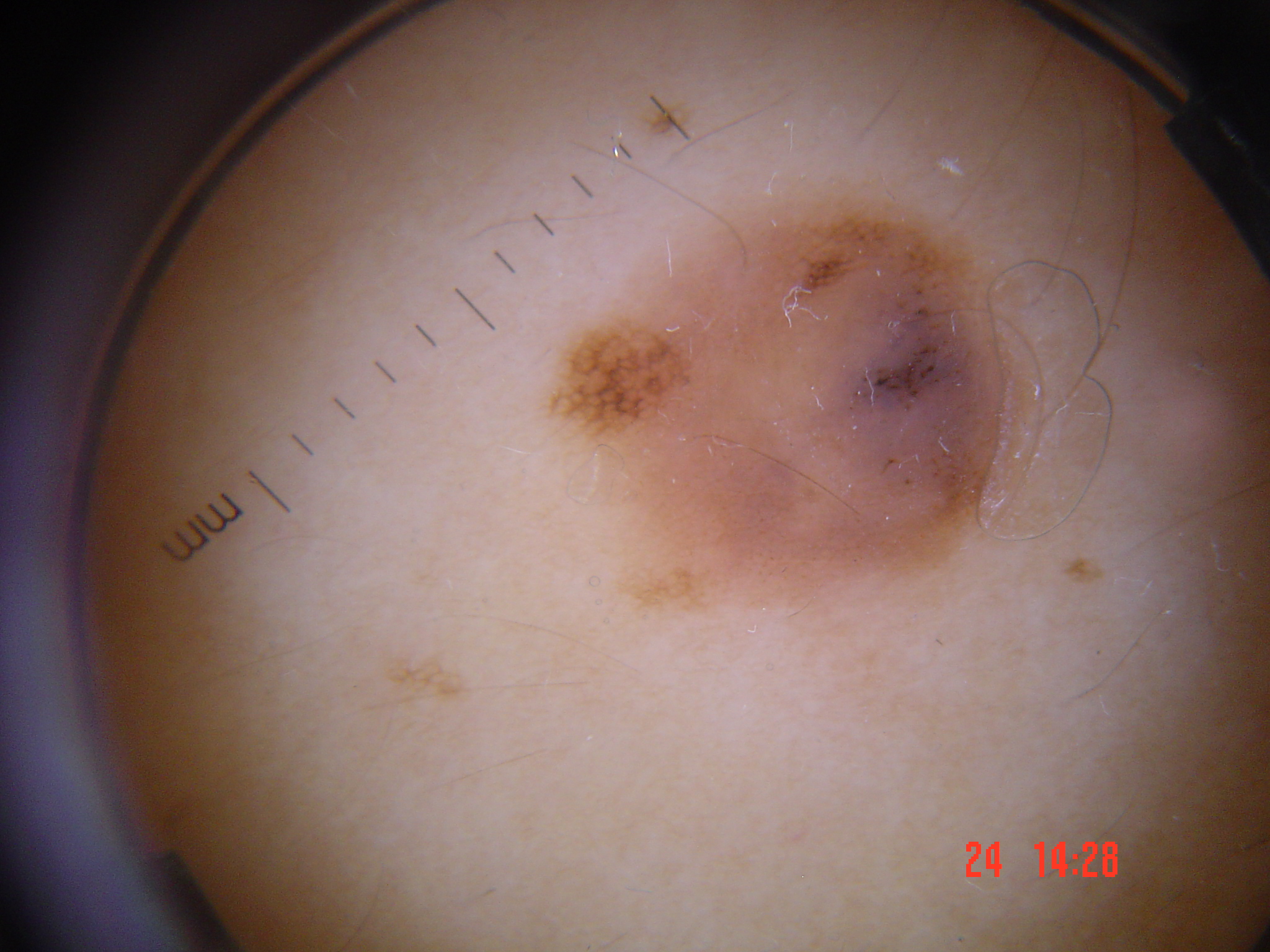A skin lesion imaged with a dermatoscope.
The diagnostic label was a congenital compound nevus.